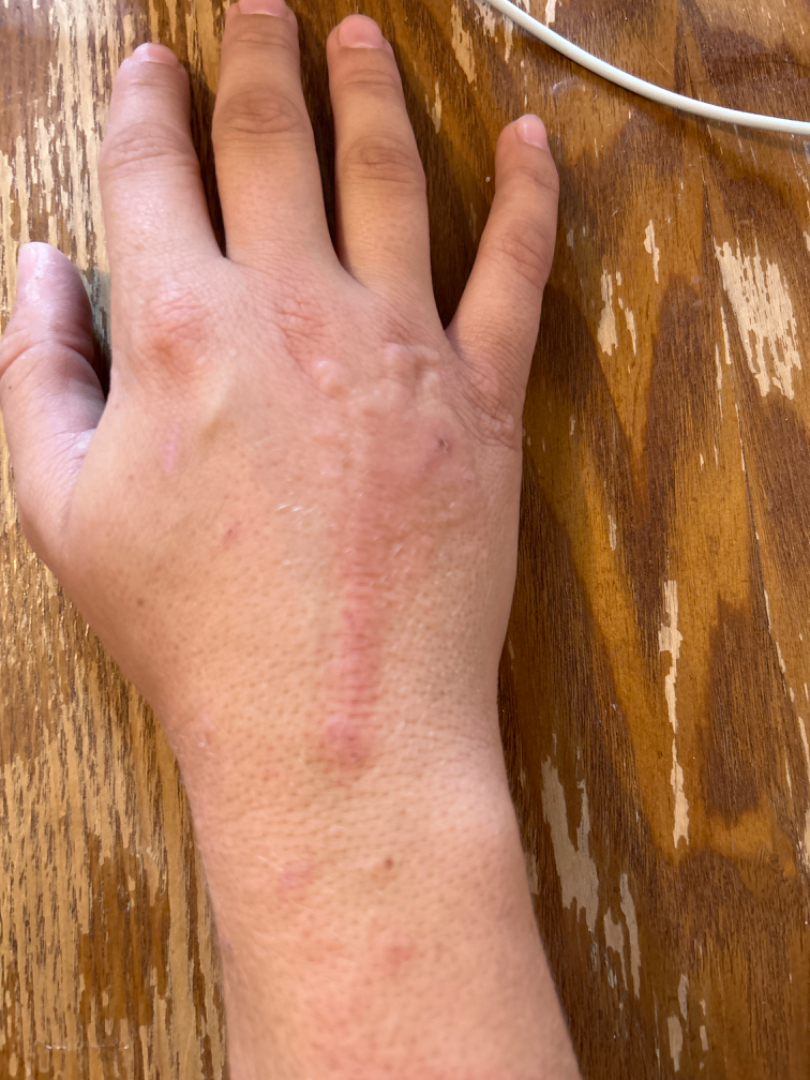| feature | finding |
|---|---|
| site | top or side of the foot, head or neck, back of the hand and leg |
| lesion symptoms | burning, pain, enlargement, darkening, itching and bothersome appearance |
| image framing | close-up |
| subject | female, age 18–29 |
| history | one to four weeks |
| surface texture | raised or bumpy |
| impression | Contact dermatitis (primary); Cat scratch disease (possible); Cutaneous sarcoidosis (possible); Deep fungal infection (possible) |